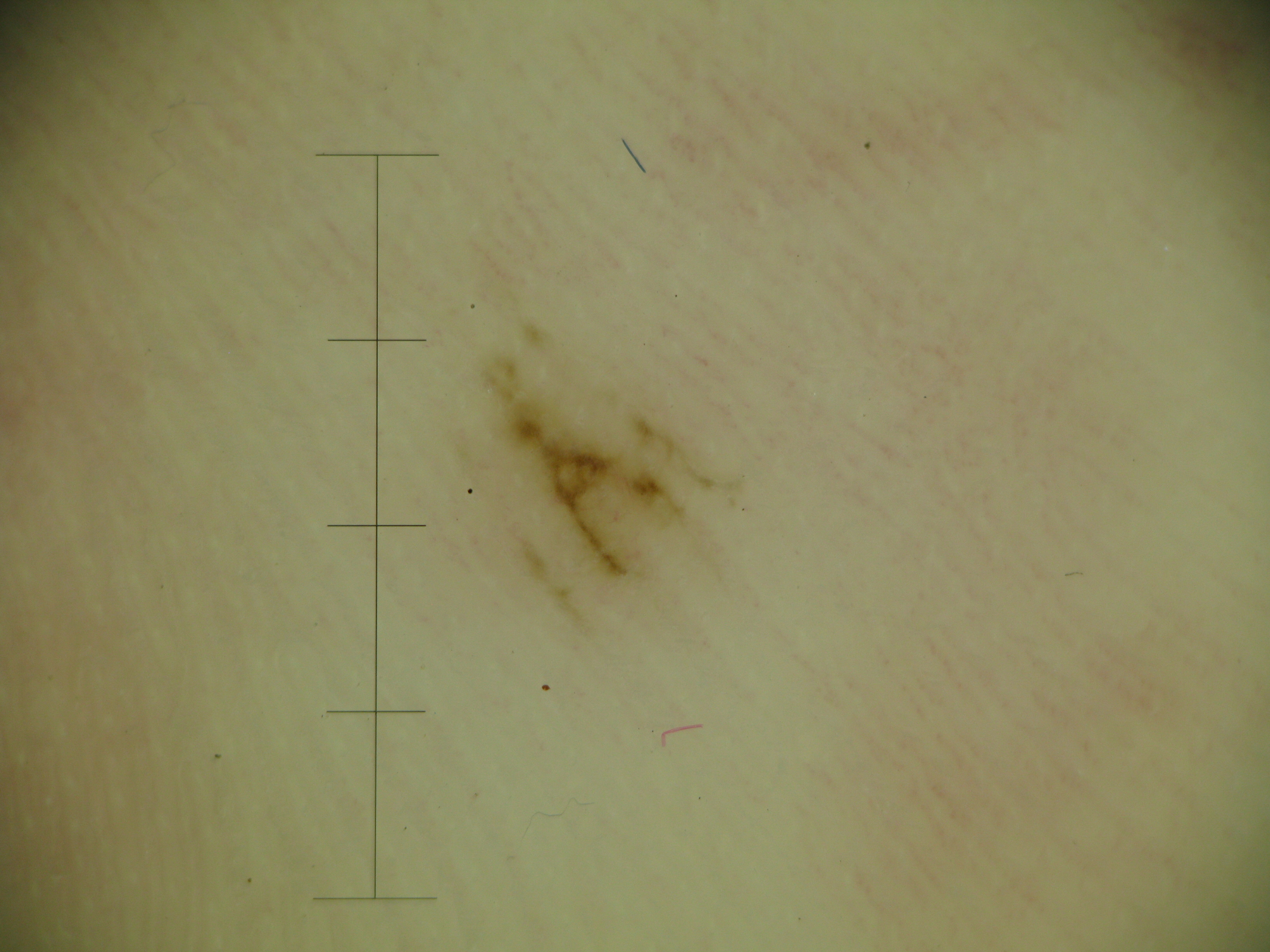Summary: A dermatoscopic image of a skin lesion. Conclusion: The diagnosis was a banal lesion — an acral junctional nevus.